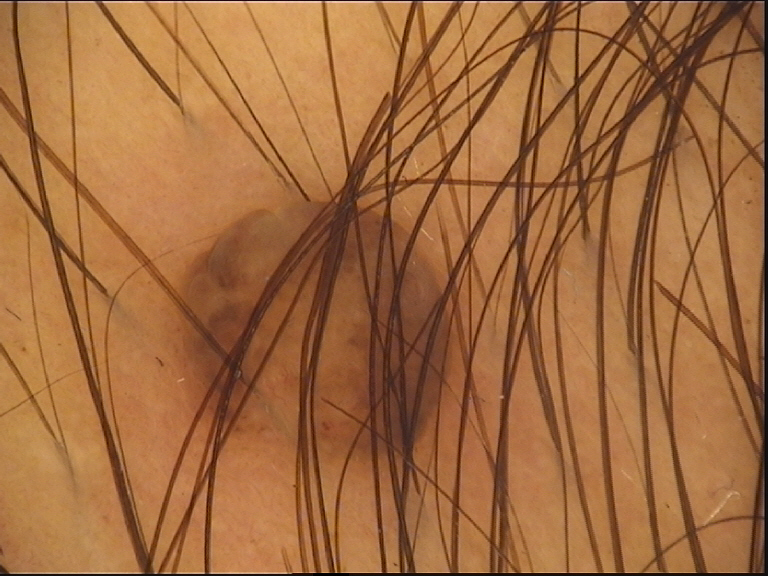<lesion>
  <diagnosis>
    <name>dermal nevus</name>
    <code>db</code>
    <malignancy>benign</malignancy>
    <super_class>melanocytic</super_class>
    <confirmation>expert consensus</confirmation>
  </diagnosis>
</lesion>